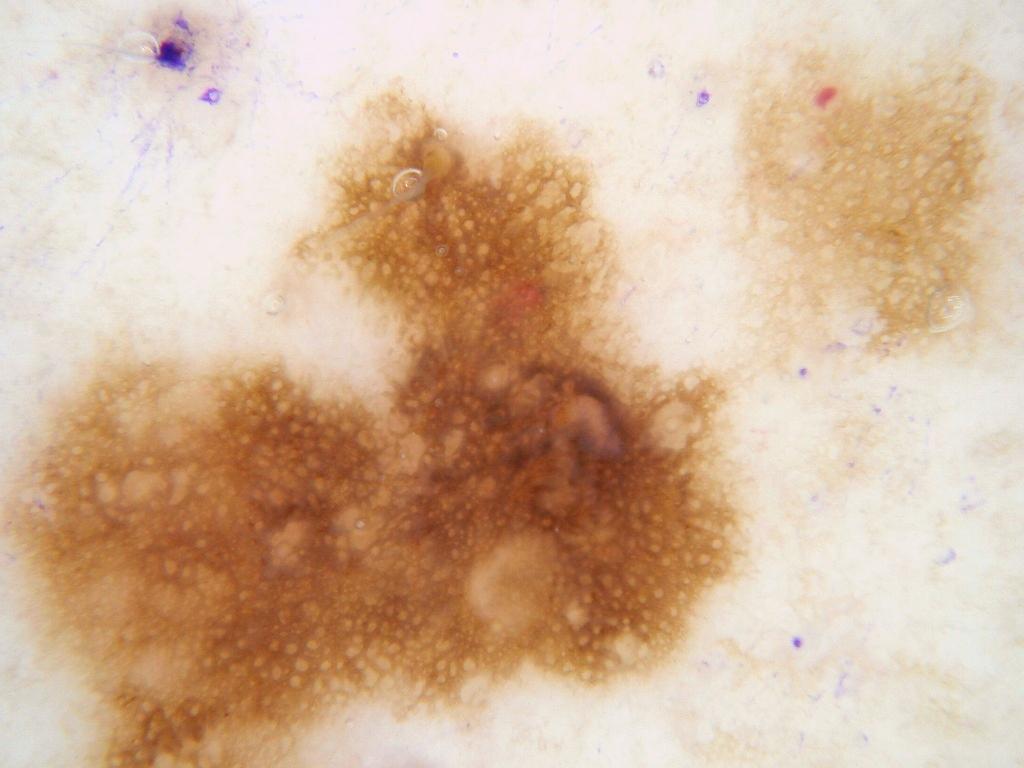The subject is a male in their mid-50s. A dermoscopy image of a single skin lesion. On dermoscopy, the lesion shows pigment network, with no milia-like cysts, streaks, globules, or negative network. The lesion extends across the full dermoscopic field. The clinical diagnosis was a melanocytic nevus.